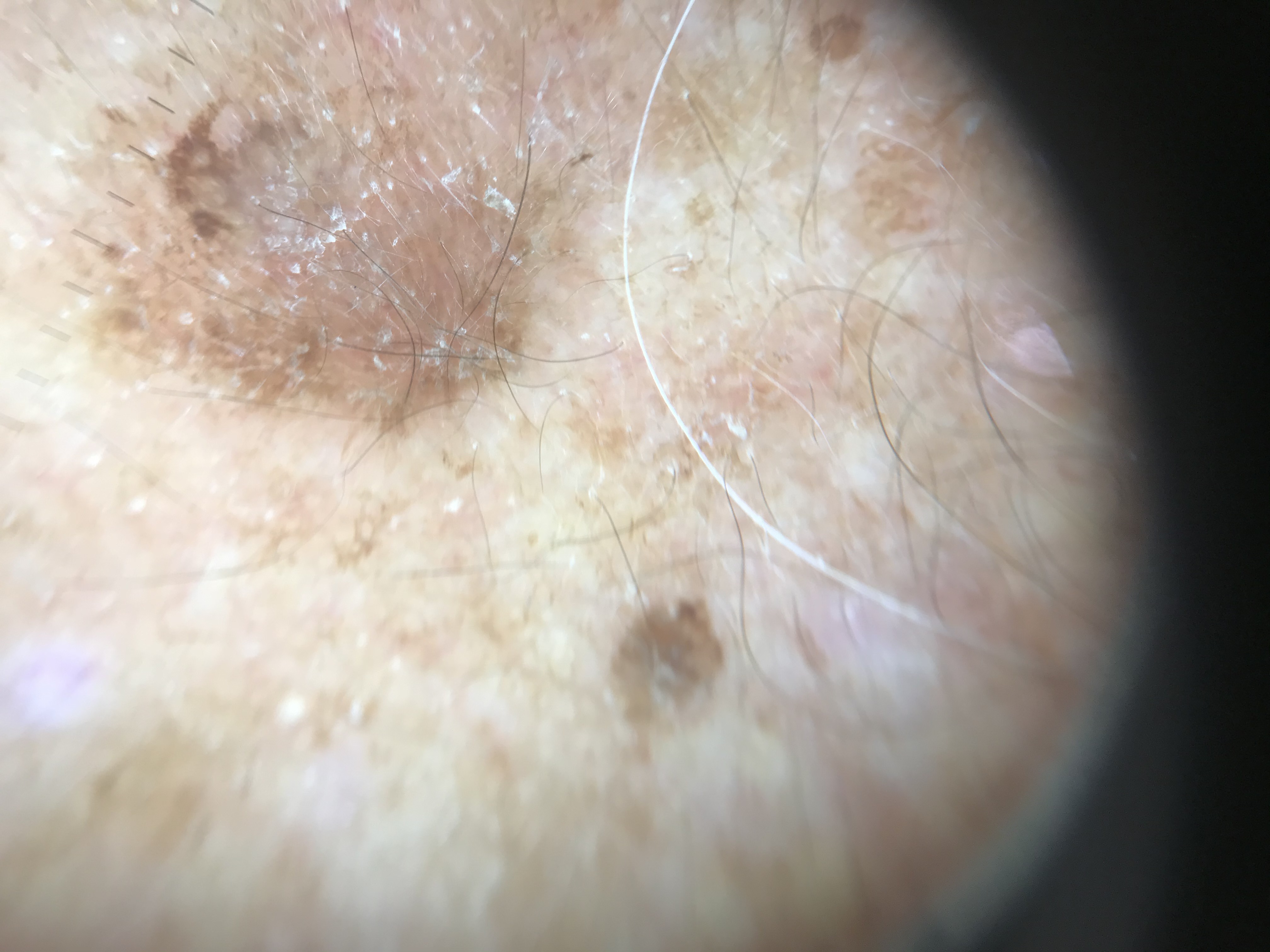<lesion>
<diagnosis>
<name>actinic keratosis</name>
<code>ak</code>
<malignancy>indeterminate</malignancy>
<super_class>non-melanocytic</super_class>
<confirmation>expert consensus</confirmation>
</diagnosis>
</lesion>